A dermatoscopic image of a skin lesion: 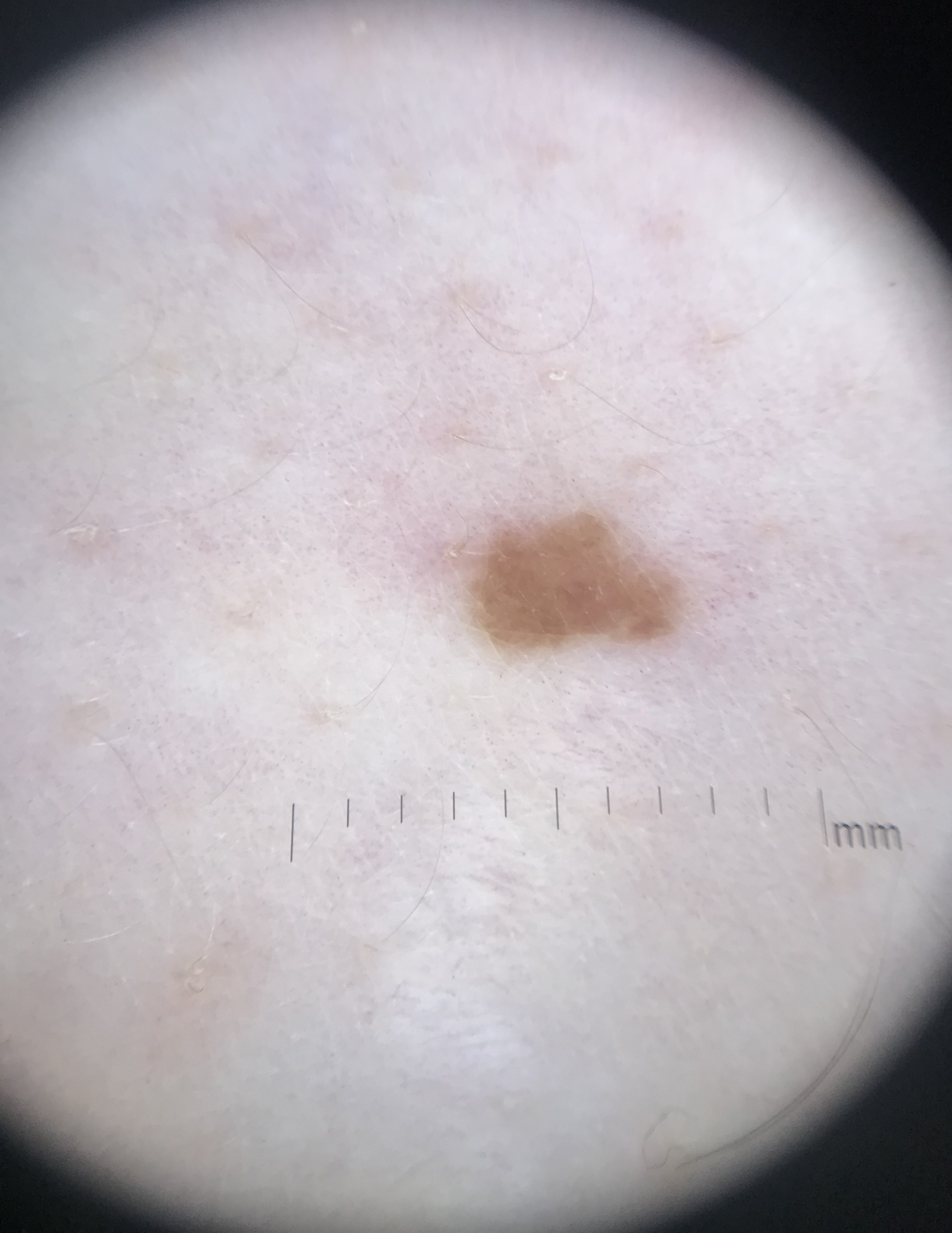diagnostic label: seborrheic keratosis (expert consensus)